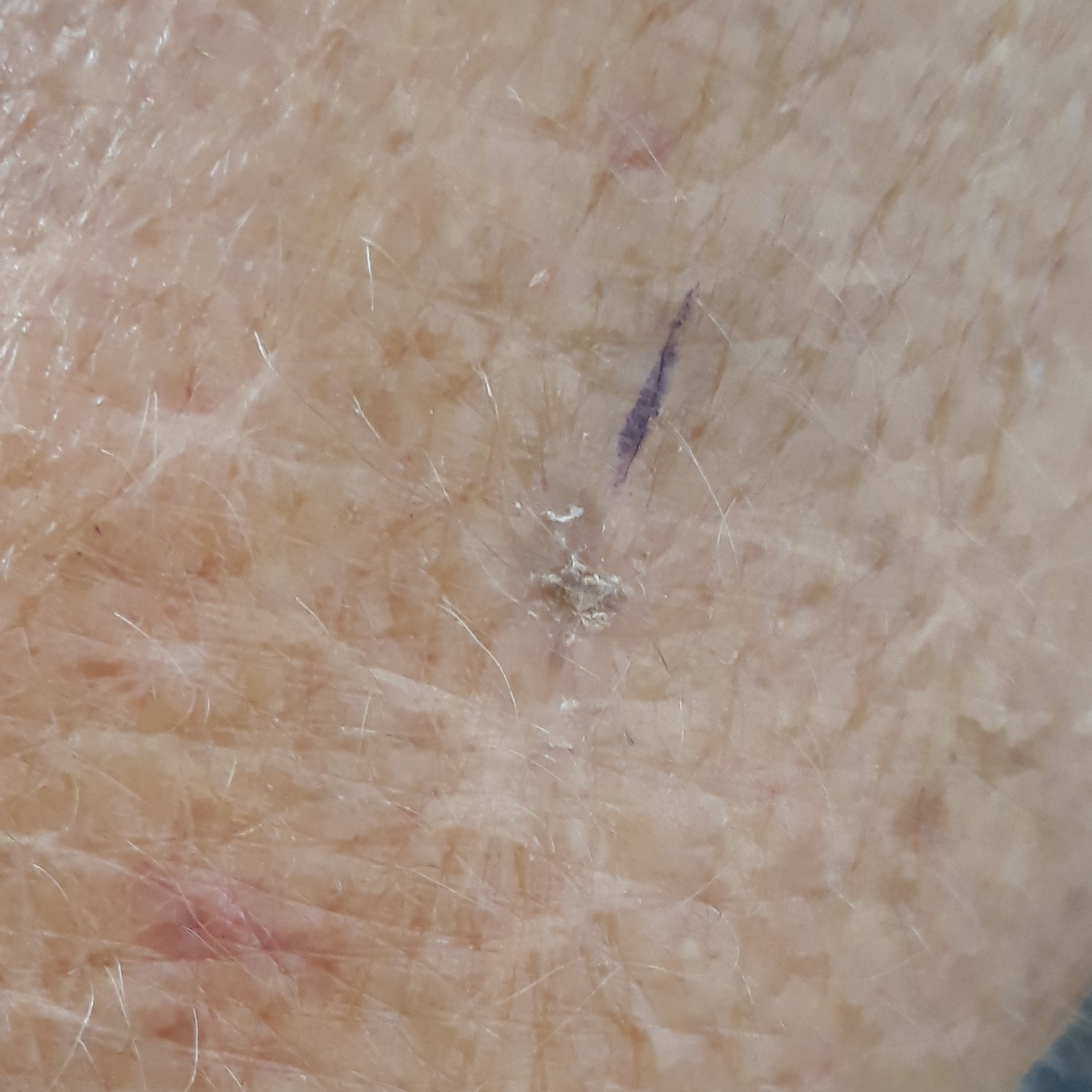Notes:
* subject — in their 60s
* site — a forearm
* patient-reported symptoms — growth, change in appearance, elevation
* assessment — actinic keratosis (clinical consensus)